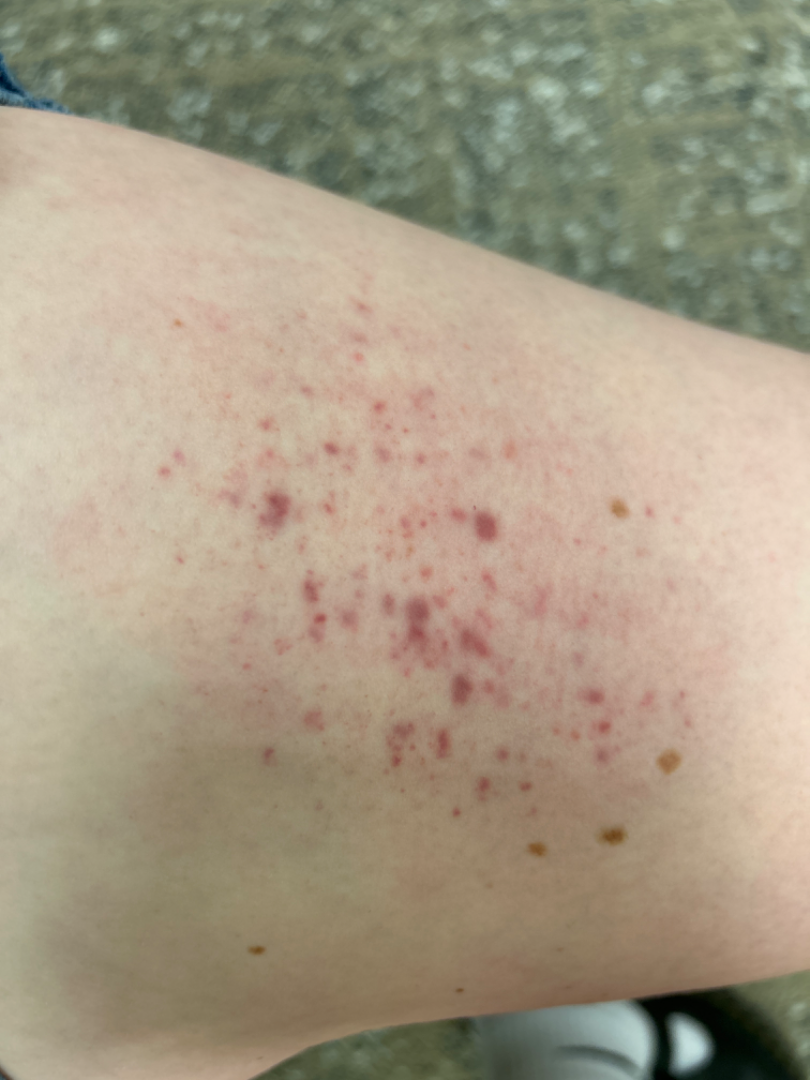Q: Anatomic location?
A: leg
Q: How does the lesion feel?
A: flat
Q: Patient demographics?
A: female, age 18–29
Q: Reported symptoms?
A: bothersome appearance
Q: Image view?
A: close-up
Q: How does the patient describe it?
A: a pigmentary problem
Q: What conditions are considered?
A: in keeping with Purpura